The contributor reports associated fatigue and chills, symptoms reported: bothersome appearance and itching, an image taken at an angle, the patient described the issue as a rash, the affected area is the arm and back of the hand, texture is reported as rough or flaky and raised or bumpy.
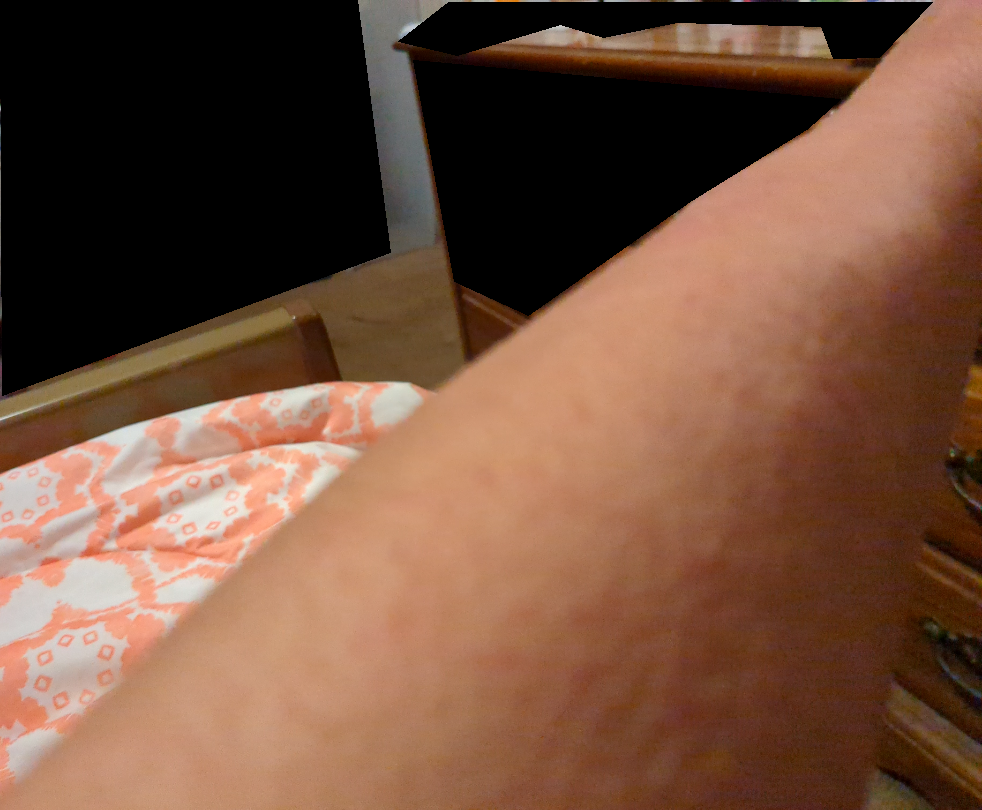dermatologist impression: most consistent with Folliculitis; an alternative is Eczema